The back of the torso is involved · this is a close-up image.
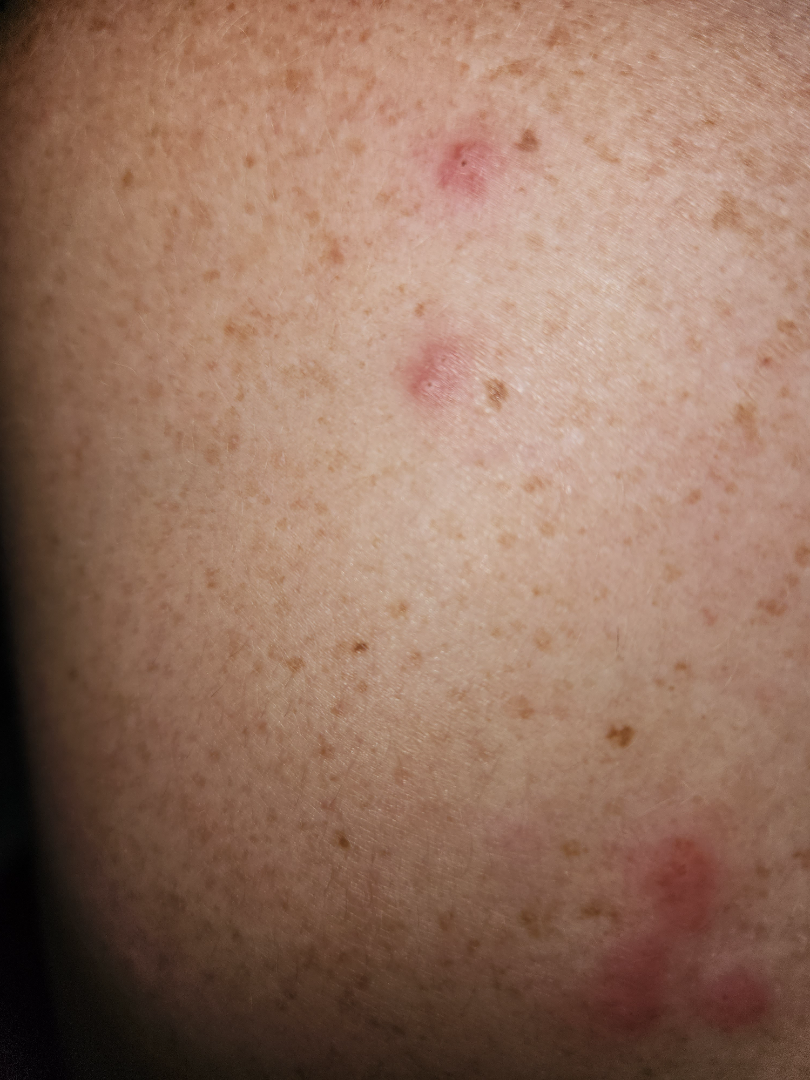assessment=indeterminate from the photograph.